A dermoscopic photograph of a skin lesion.
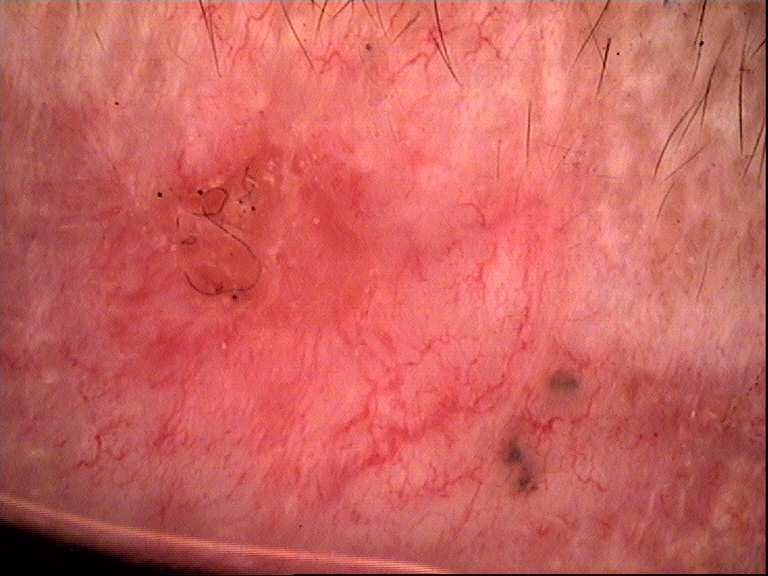Q: What did the workup show?
A: basal cell carcinoma (biopsy-proven)